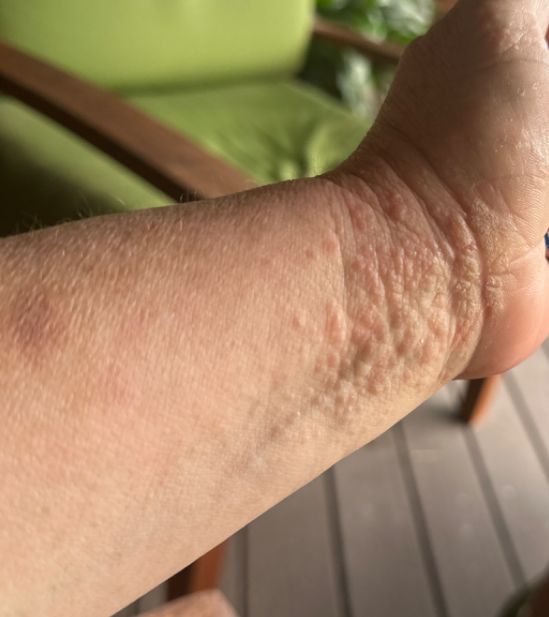Case summary:
* view — at a distance
* reported symptoms — itching and burning
* patient describes the issue as — a rash
* lesion texture — raised or bumpy and rough or flaky
* differential — the favored diagnosis is Allergic Contact Dermatitis; possibly Eczema